A close-up photograph. The affected area is the arm: 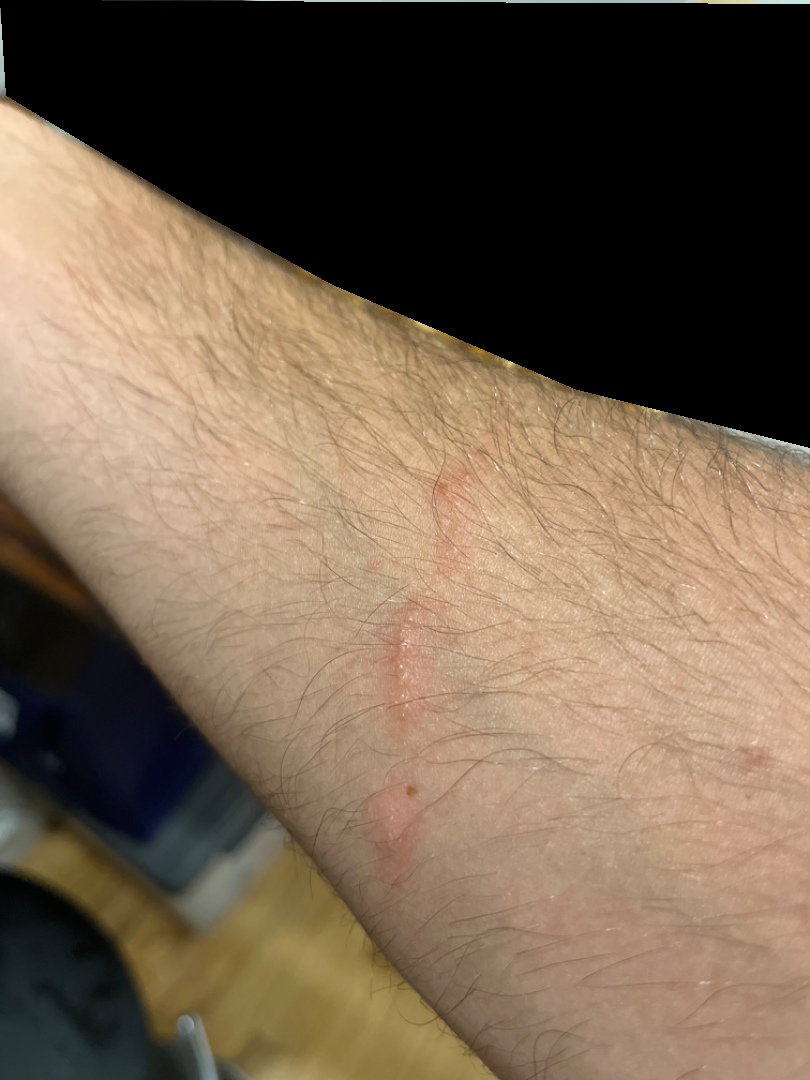assessment: unable to determine.